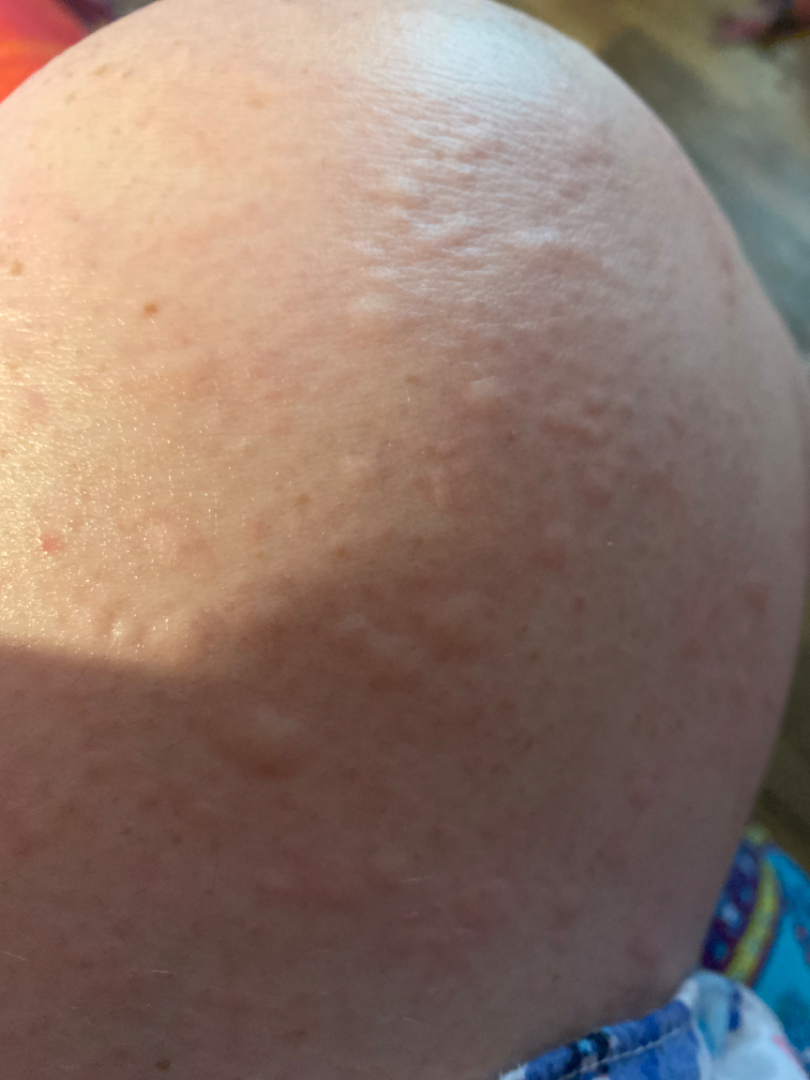photo taken = close-up, symptom duration = about one day, described texture = raised or bumpy, anatomic site = arm and leg, diagnostic considerations = Urticaria (0.55); Eczema (0.27); Leukocytoclastic Vasculitis (0.18).